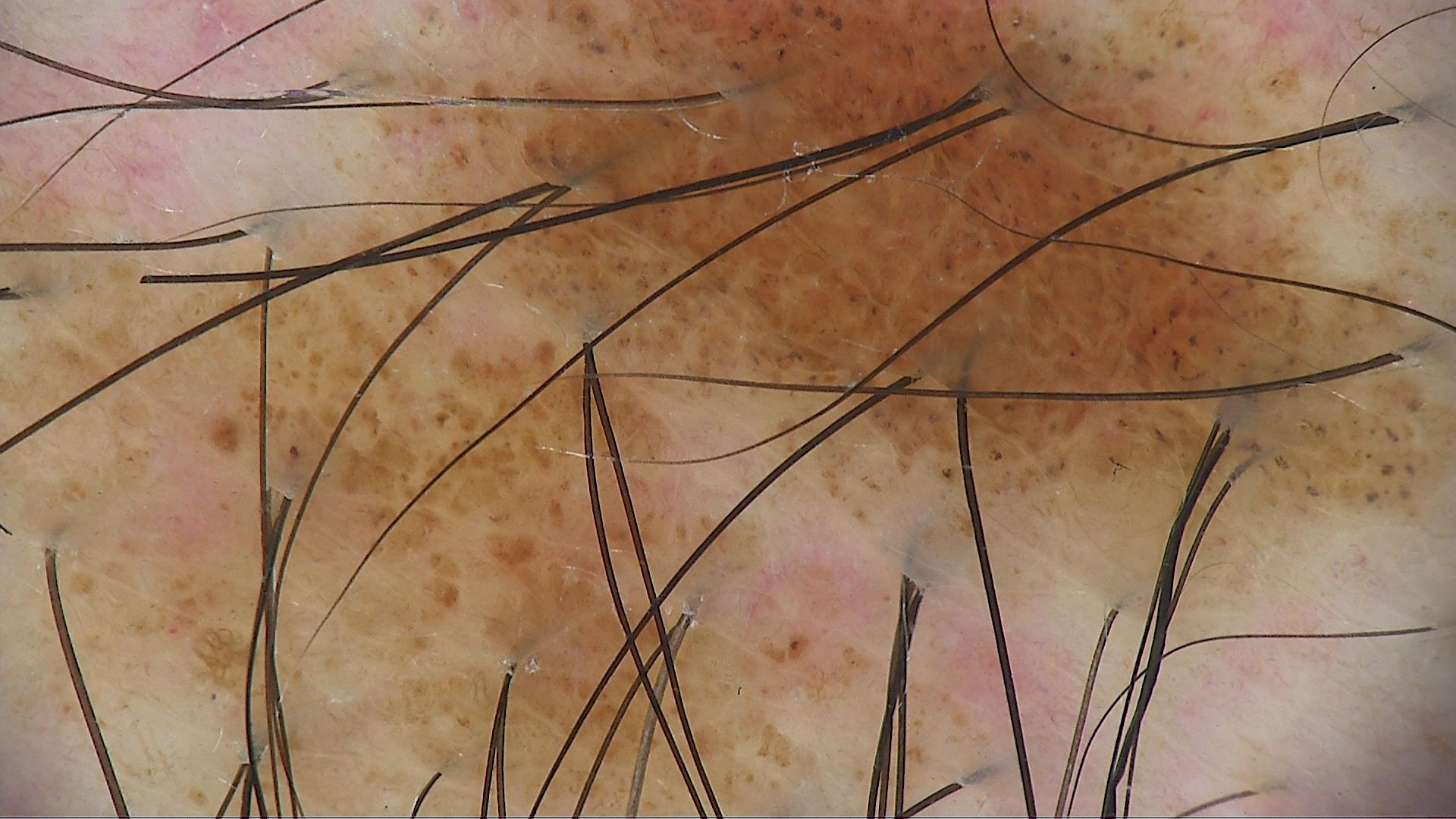Conclusion: The diagnosis was a compound nevus.